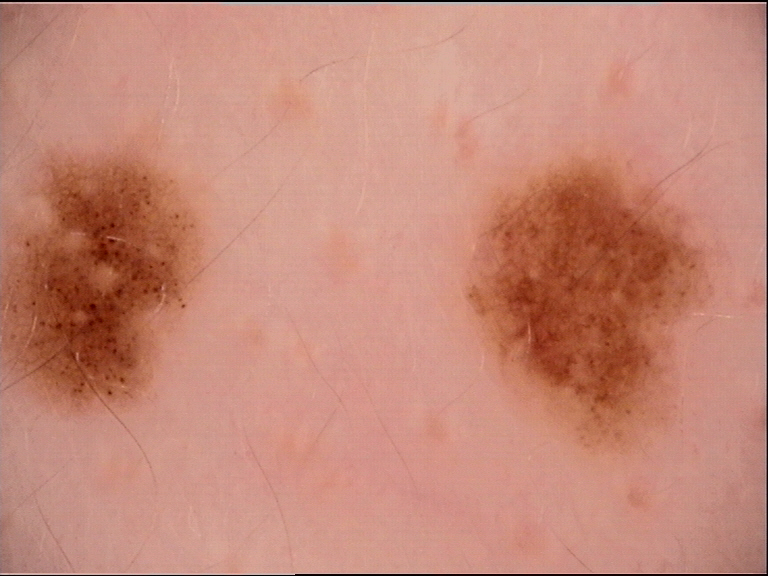Conclusion: The diagnosis was a junctional nevus.